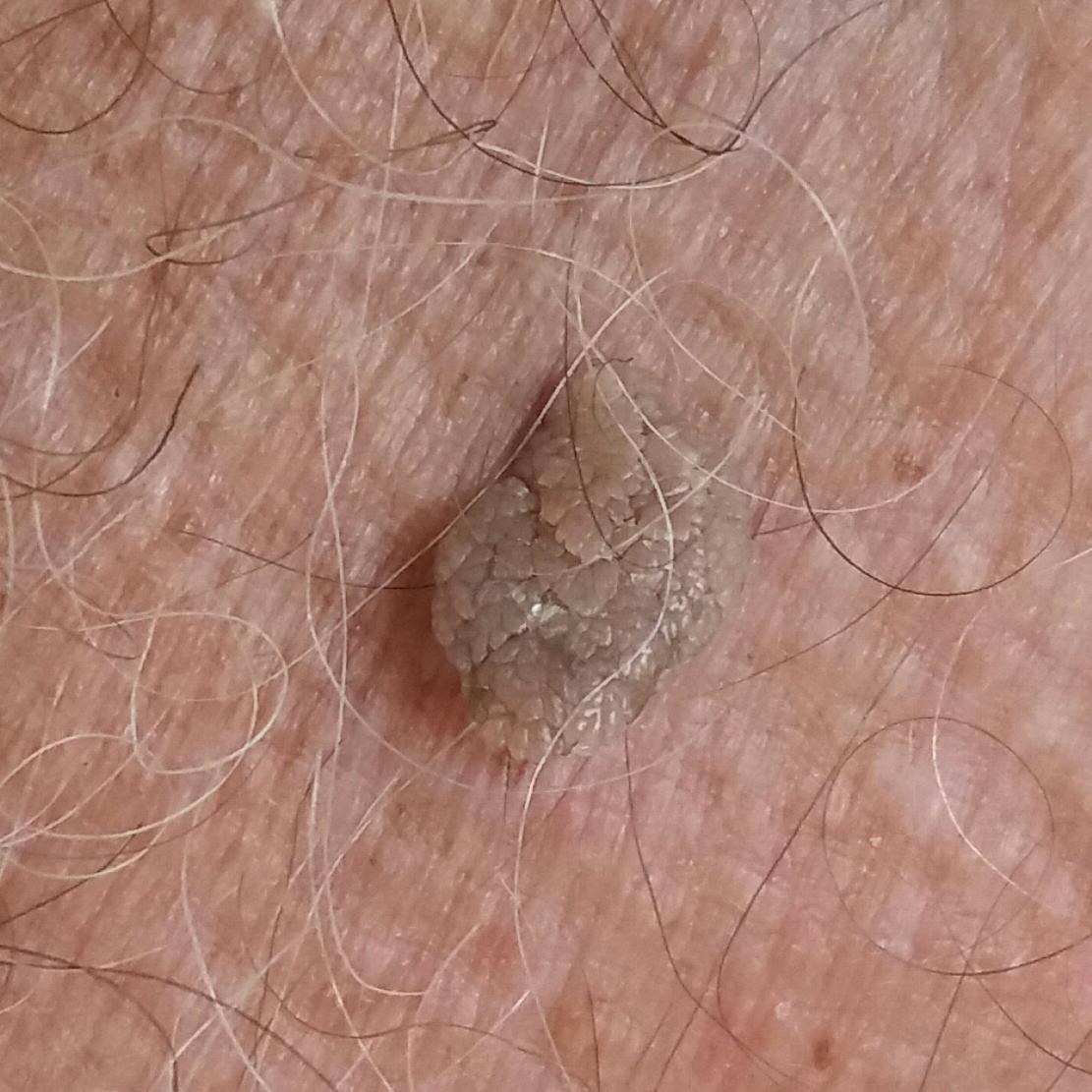  diagnosis:
    name: seborrheic keratosis
    code: SEK
    malignancy: benign
    confirmation: clinical consensus